The photo was captured at an angle; located on the arm: 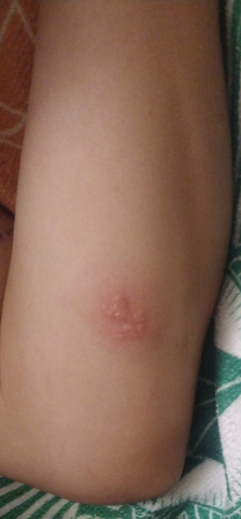Patient information:
Lay graders estimated Monk Skin Tone 2 or 3 (two reviewer pools). Self-categorized by the patient as a rash. Texture is reported as raised or bumpy and fluid-filled. Reported lesion symptoms include burning and itching. No associated systemic symptoms reported.
Review:
Allergic Contact Dermatitis (weight 0.50); Herpes Simplex (weight 0.50).